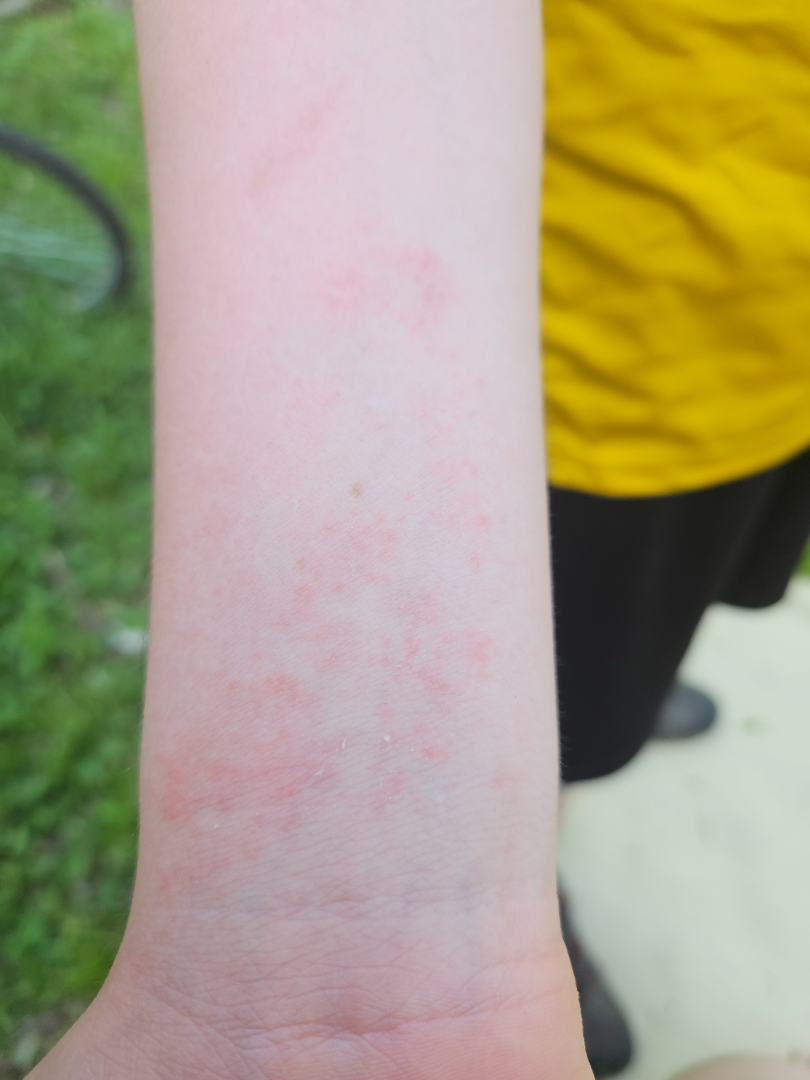{
  "body_site": "arm",
  "shot_type": "close-up",
  "differential": {
    "leading": [
      "Eczema"
    ],
    "considered": [
      "Allergic Contact Dermatitis"
    ]
  }
}